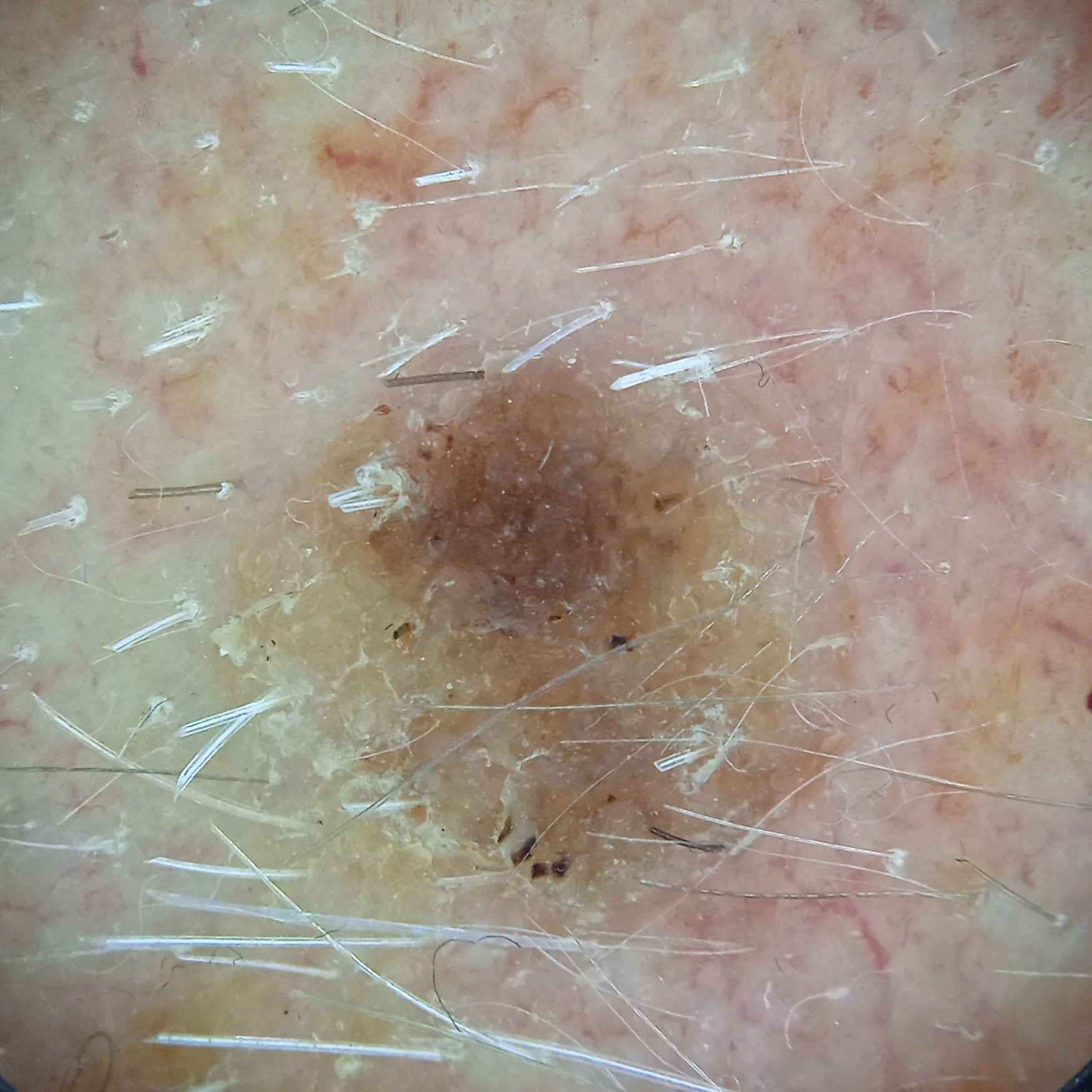Findings:
A male patient 78 years old. The patient says their skin reddens with sun exposure. By self-report, a personal history of cancer. Imaged for a research study, with no referral diagnosis recorded. Few moles overall by the patient's own estimate. Located on the face.
Assessment:
Four dermatologists reviewed the lesion; the consensus was a seborrheic keratosis; agreement among the reviewers was unanimous; diagnostic confidence was good; an alternative consideration was a melanocytic nevus.